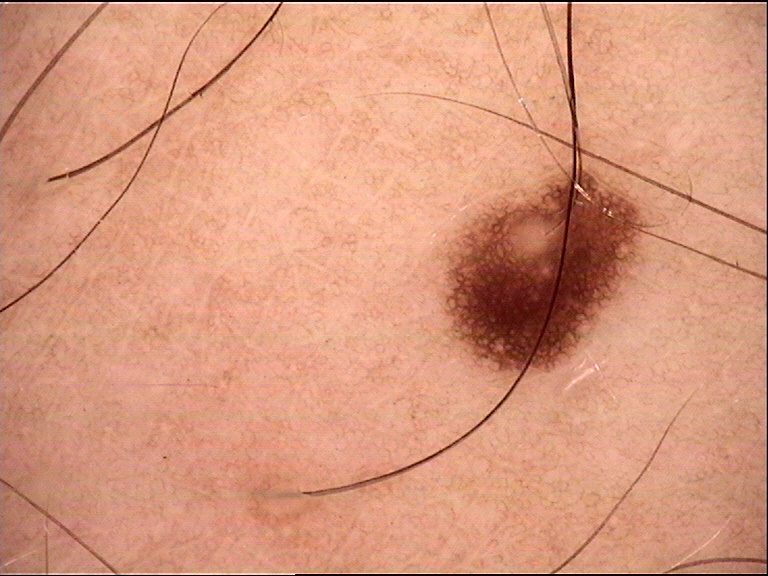The diagnosis was a junctional nevus.